A dermoscopic close-up of a skin lesion. Fitzpatrick II. The chart documents a previous melanoma.
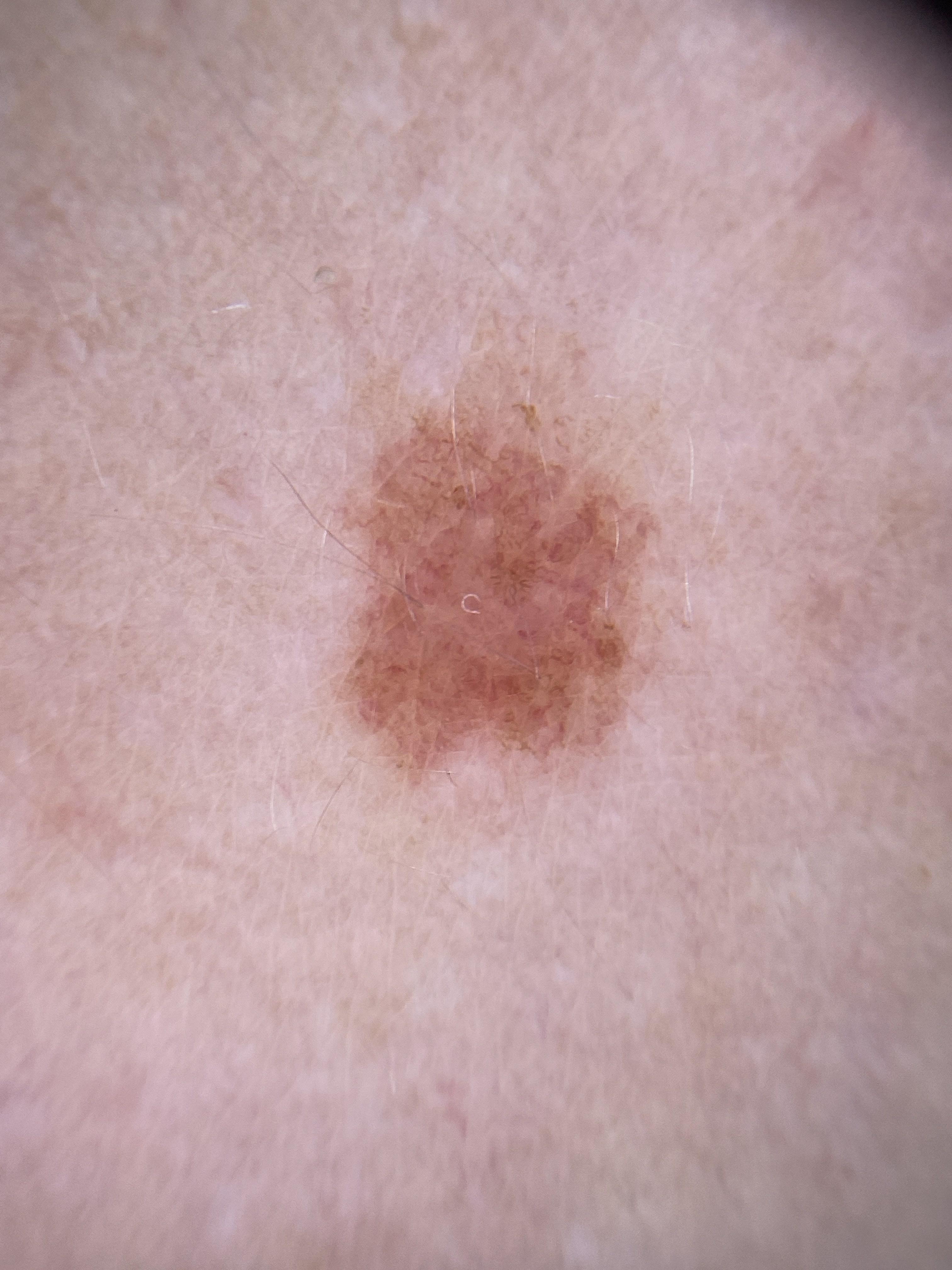The lesion is on the posterior trunk. Clinically diagnosed as a nevus.